A skin lesion imaged with contact-polarized dermoscopy: 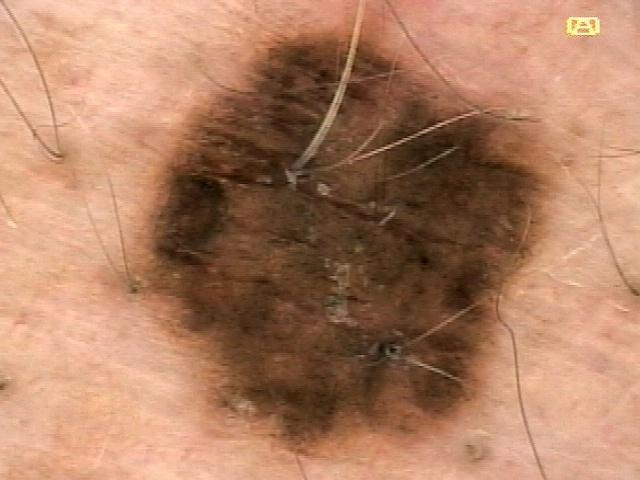Summary: The lesion involves the trunk, specifically the posterior trunk. Conclusion: The biopsy diagnosis was a melanoma.